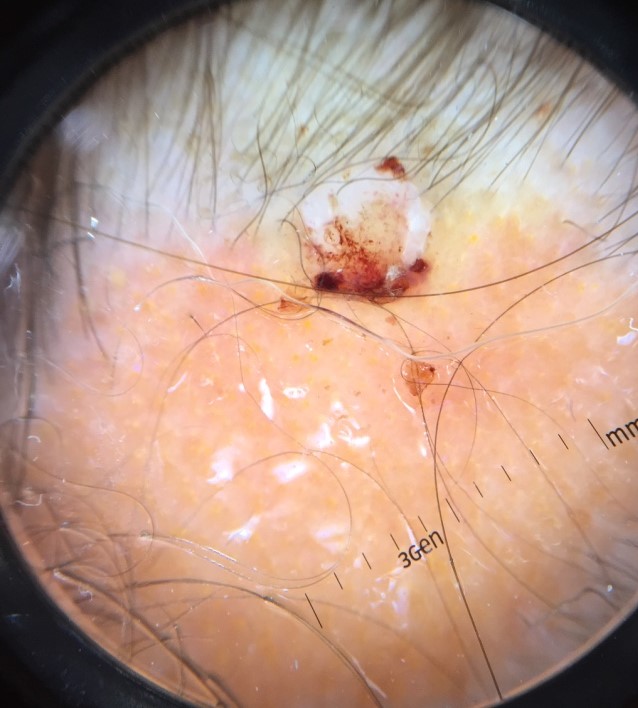label: squamous cell carcinoma (biopsy-proven).